A dermatoscopic image of a skin lesion:
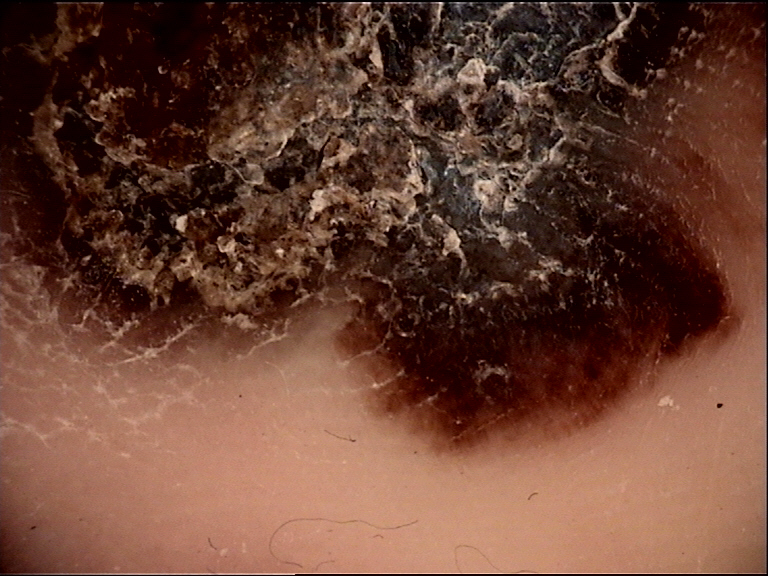Findings:
– label — acral lentiginous melanoma (biopsy-proven)